The photograph is a close-up of the affected area — 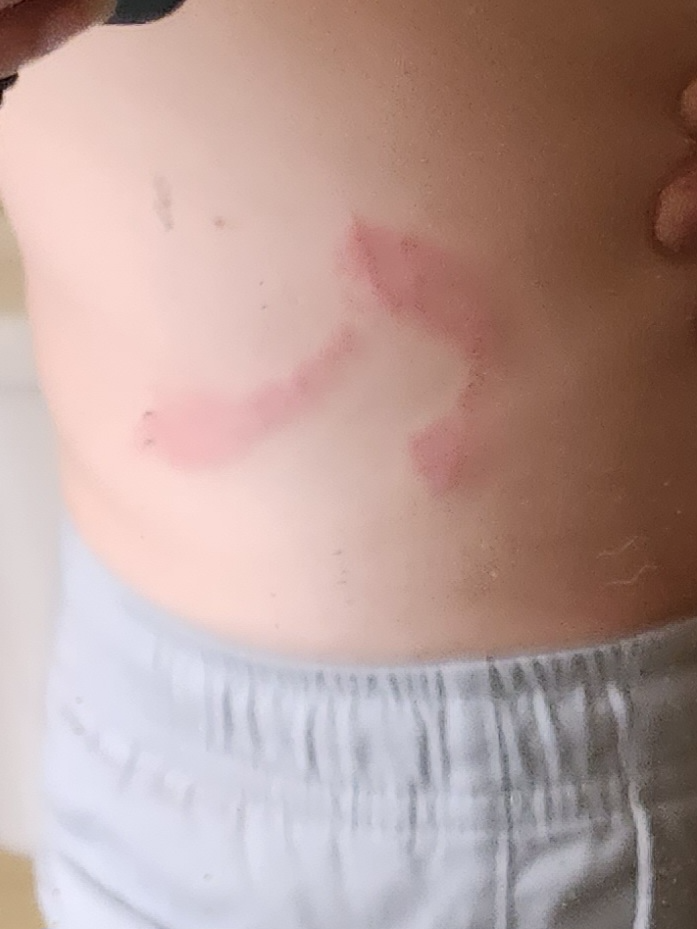| field | value |
|---|---|
| assessment | unable to determine |